The affected area is the arm and leg; an image taken at an angle:
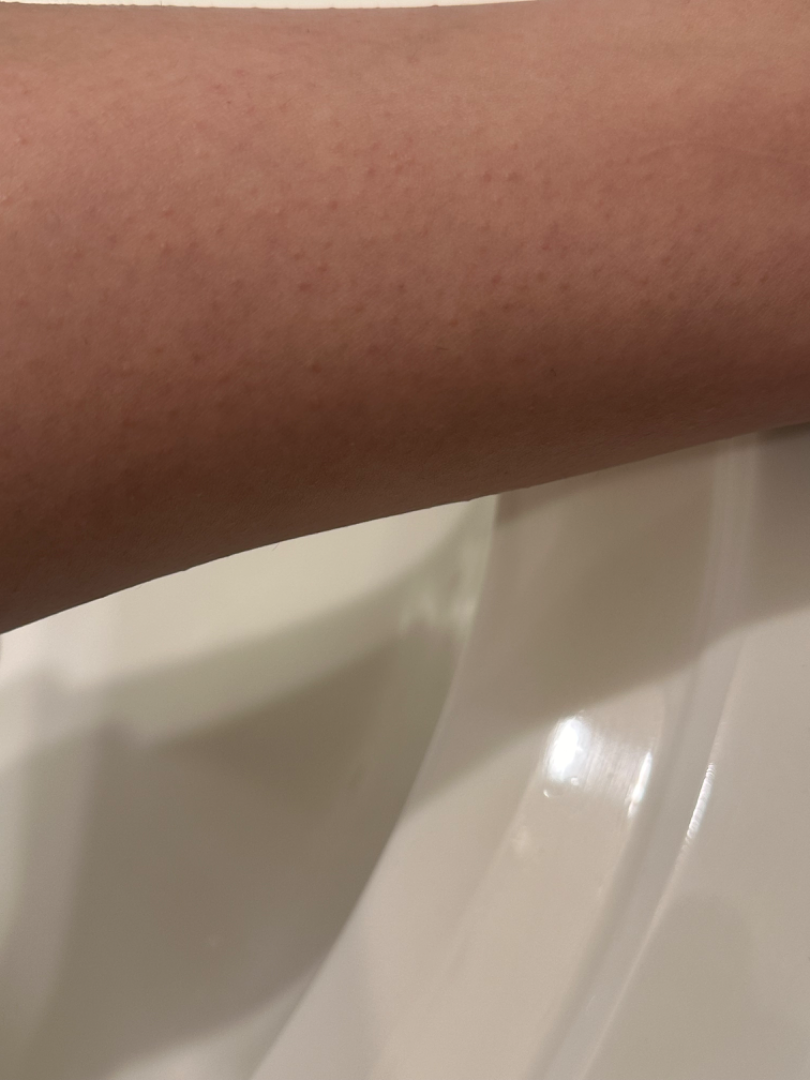differential diagnosis: Drug Rash, Viral Exanthem and Hypersensitivity were each considered, in no particular order